The subject is 60–69, female. Symptoms reported: pain, itching and burning. The lesion involves the arm, back of the torso, leg and front of the torso. An image taken at an angle. The patient described the issue as a rash. The condition has been present for one to four weeks. No relevant systemic symptoms. The patient notes the lesion is raised or bumpy — 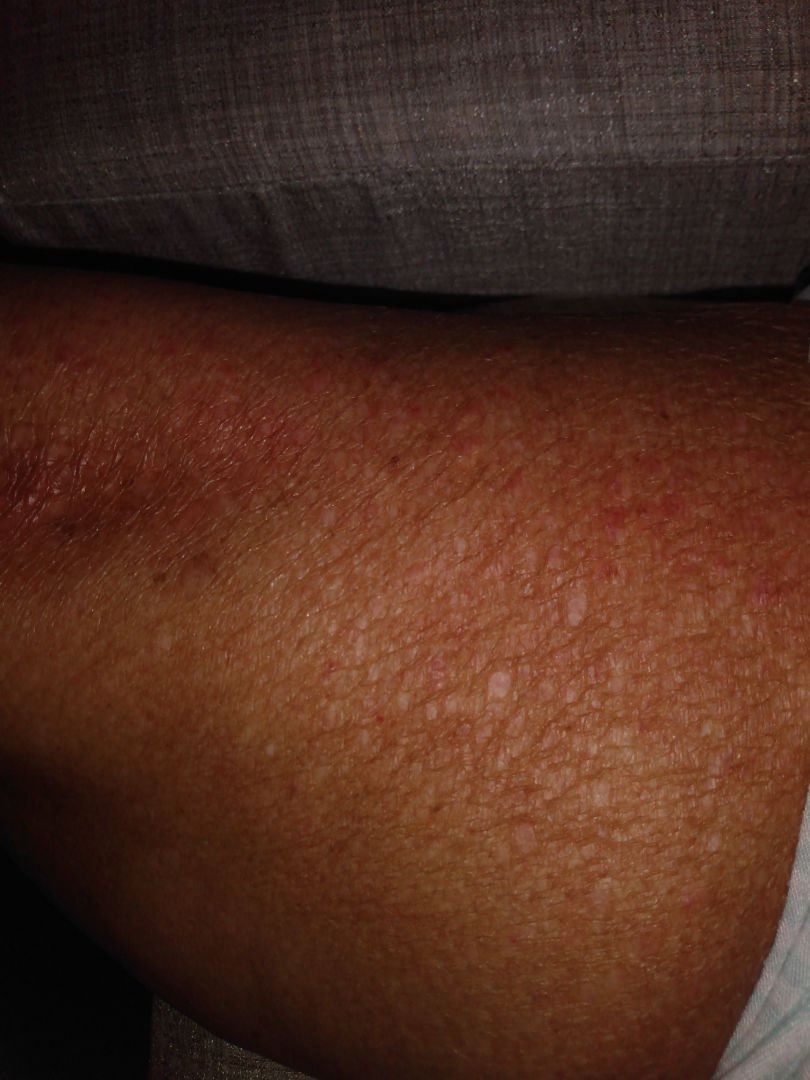assessment: could not be assessed